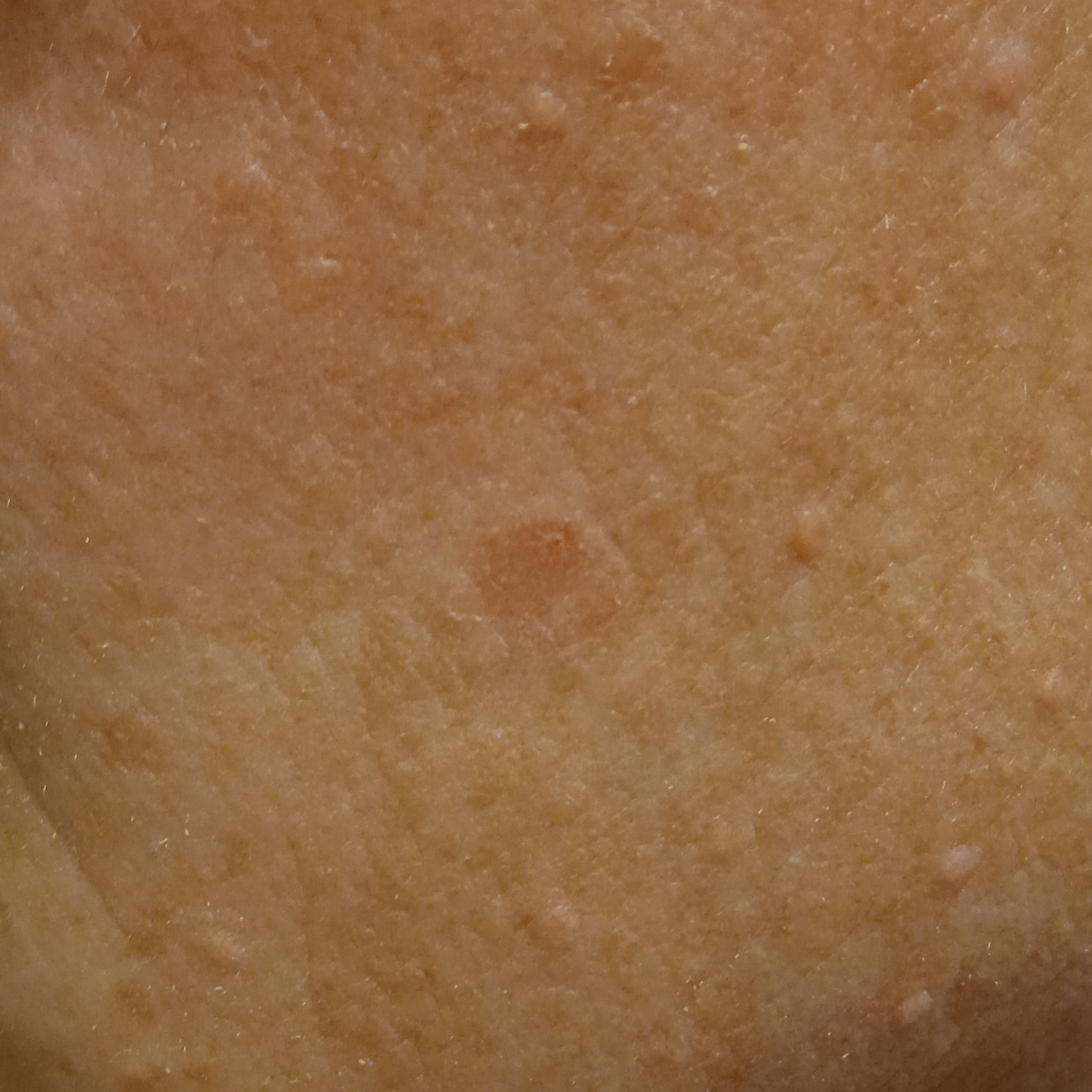Summary: A female patient 55 years old. By self-report, a prior organ transplant, immunosuppression, no personal history of skin cancer, and no family history of skin cancer. A clinical close-up of a skin lesion. Located on the face. The lesion measures approximately 5.7 mm. Conclusion: Dermatologist review favored an actinic keratosis.